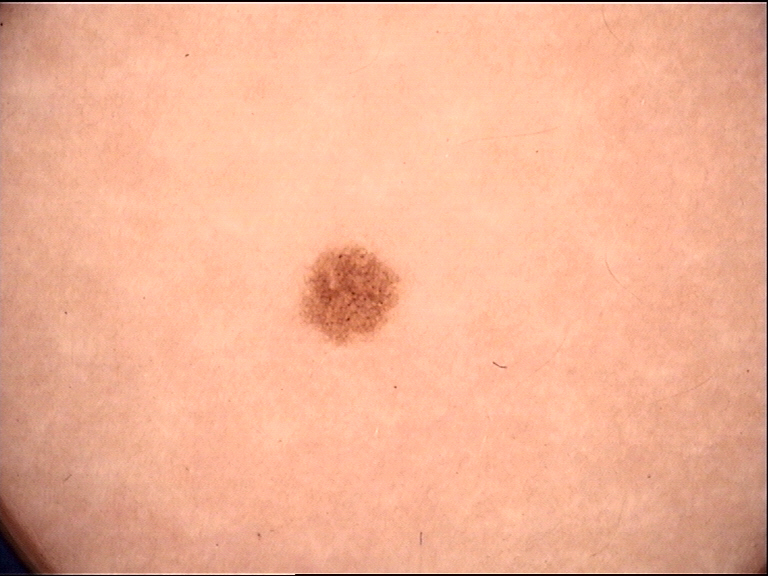image = dermatoscopy | class = dysplastic junctional nevus (expert consensus).